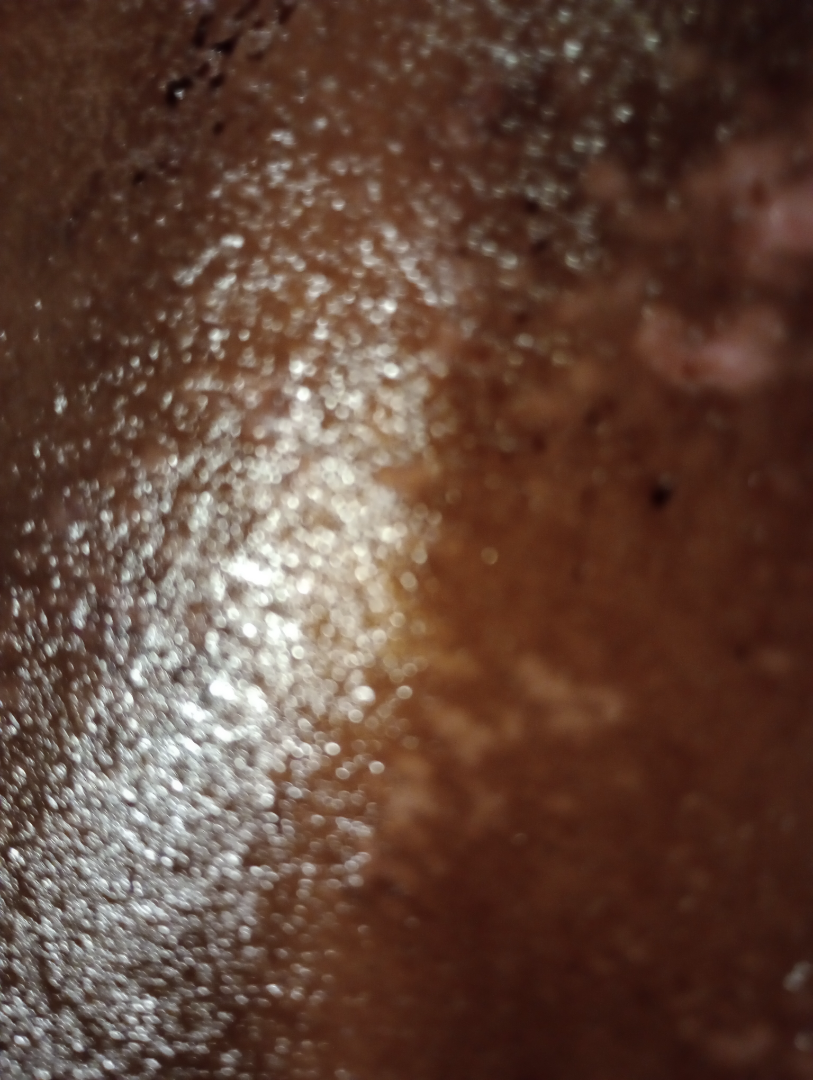Q: What was the assessment?
A: not assessable